A dermoscopic image of a skin lesion.
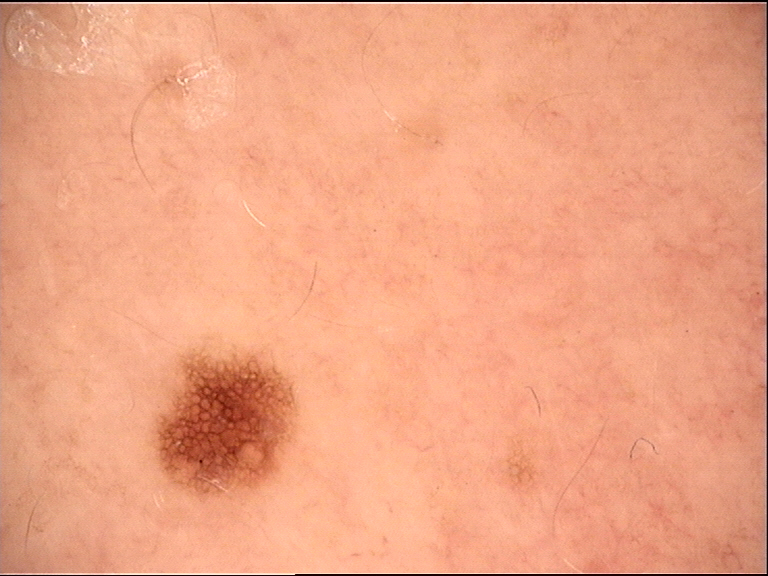Case:
- diagnostic label — dysplastic junctional nevus (expert consensus)